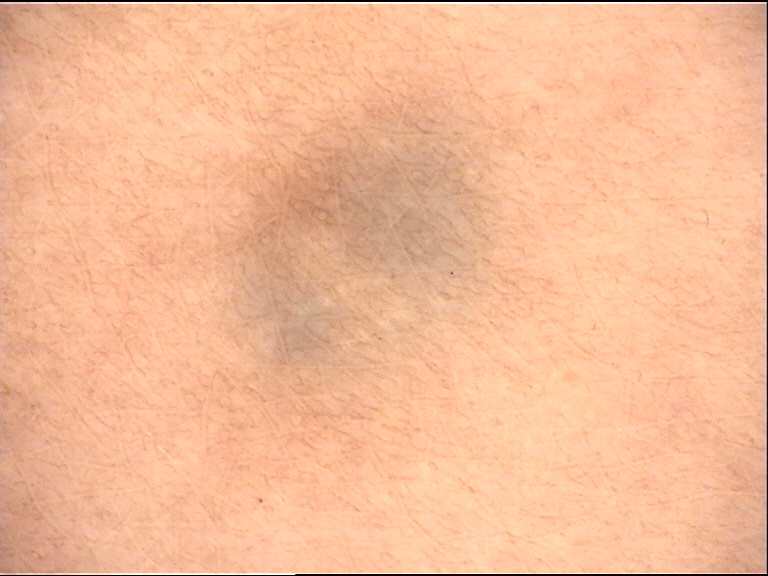Q: What is the imaging modality?
A: dermatoscopy
Q: What was the diagnostic impression?
A: blue nevus (expert consensus)